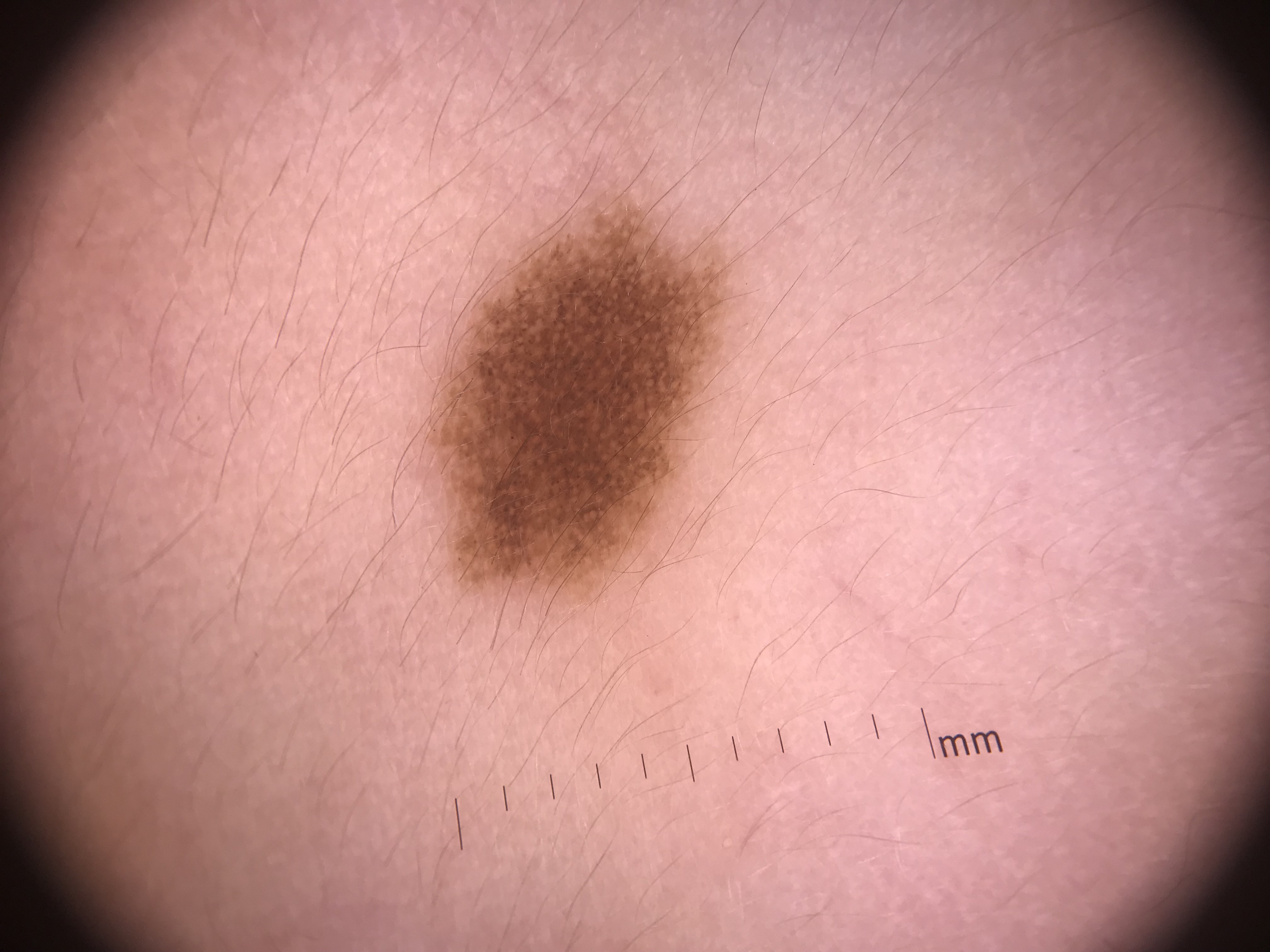Summary: A skin lesion imaged with a dermatoscope. The architecture is that of a banal lesion. Conclusion: Consistent with a junctional nevus.